Dermoscopy of a skin lesion.
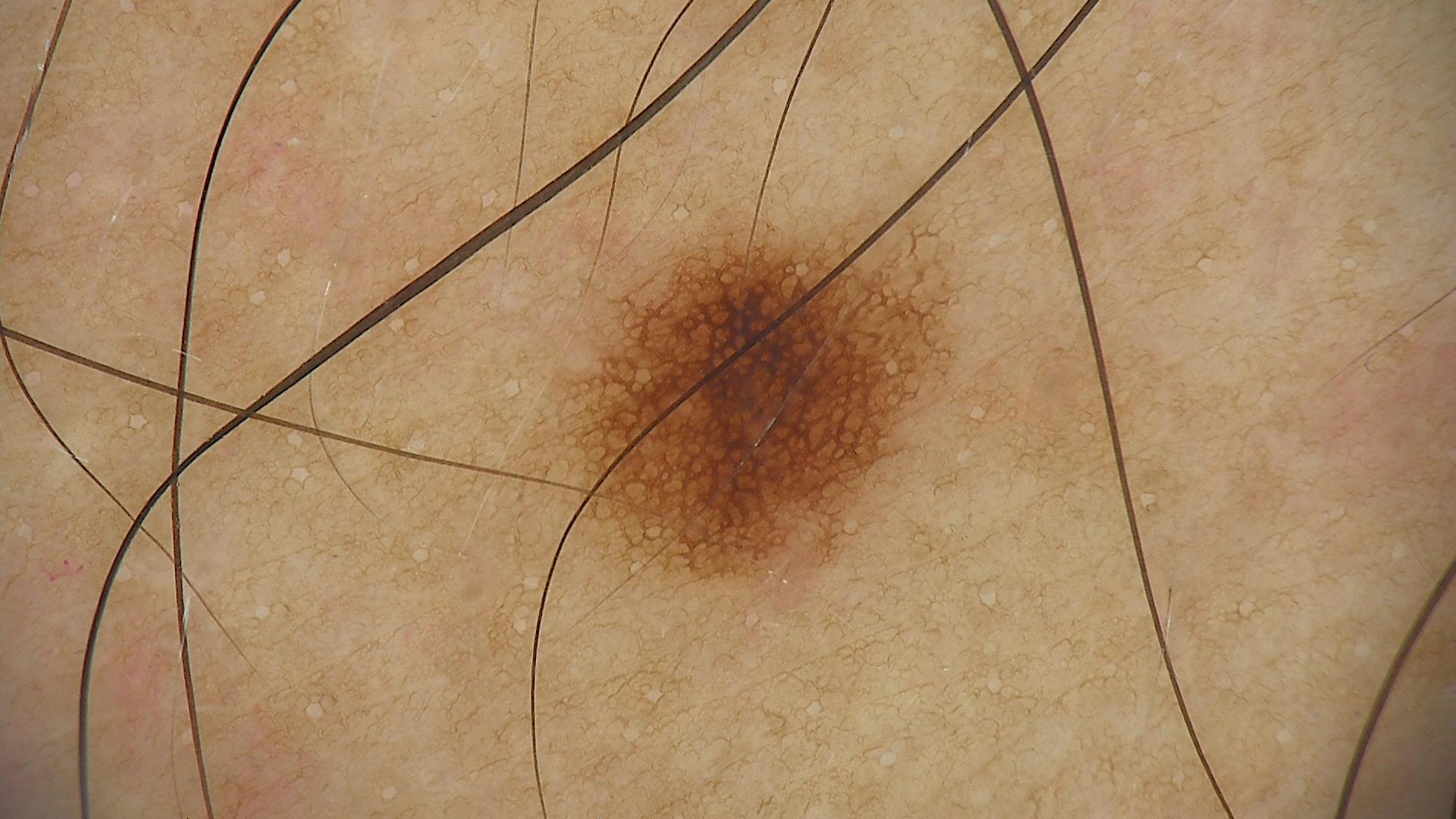label: dysplastic junctional nevus (expert consensus)